The photograph was taken at an angle.
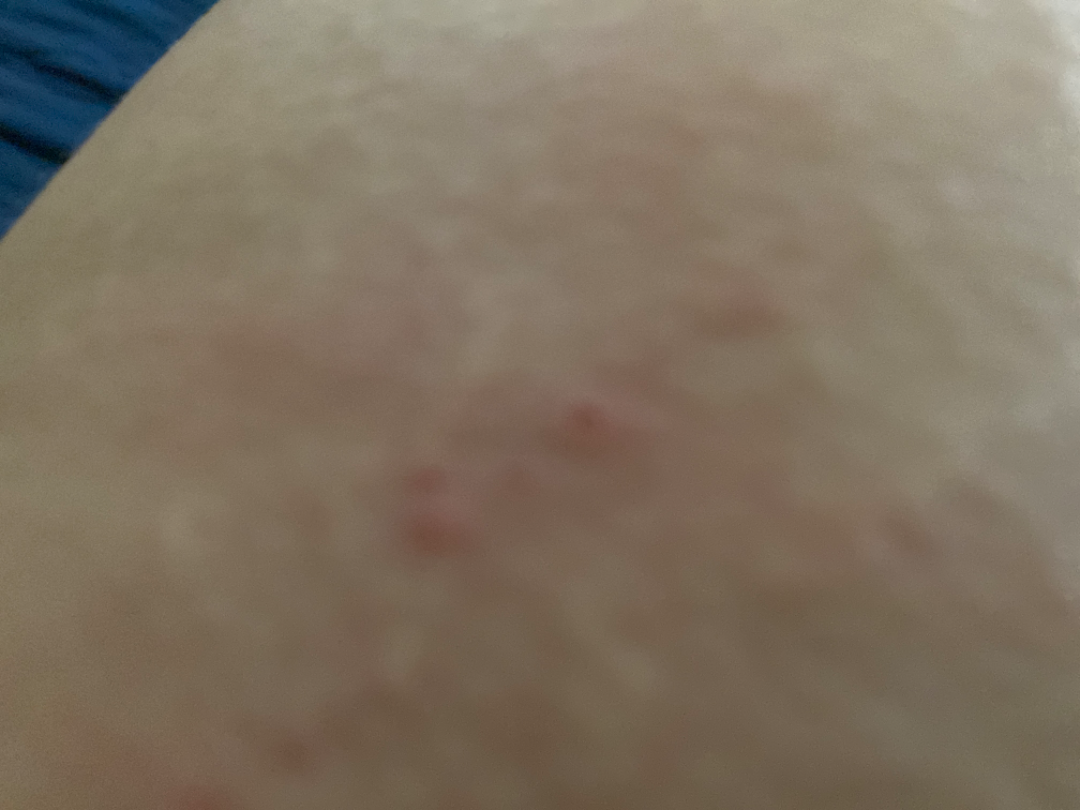On photographic review by a dermatologist: most consistent with Eczema; possibly Contact dermatitis, NOS; less likely is Urticaria.